The patient is a female aged 40–49; the photograph is a close-up of the affected area; texture is reported as raised or bumpy and rough or flaky.
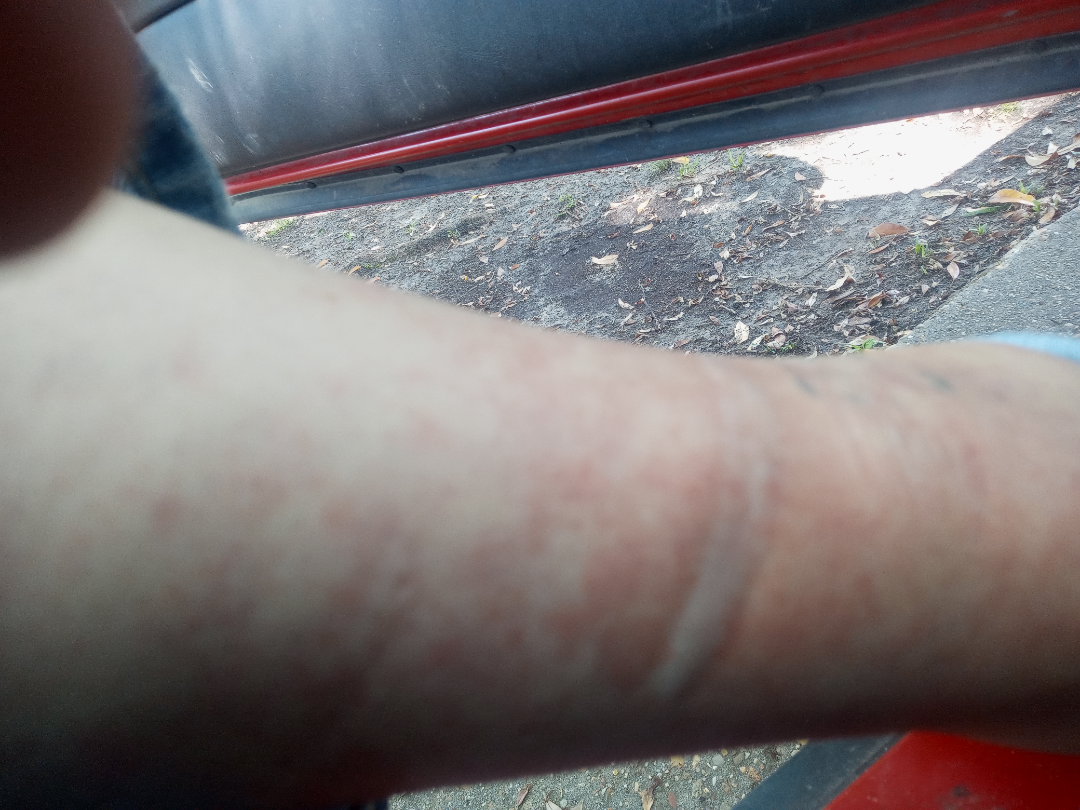Impression:
The case was indeterminate on photographic review.